A dermoscopic close-up of a skin lesion.
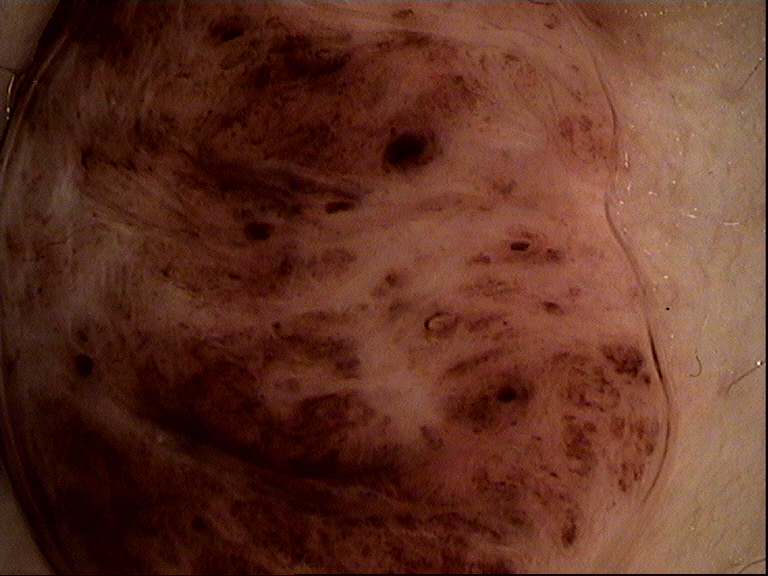Case:
- assessment: dermal nevus (expert consensus)